A dermatoscopic image of a skin lesion.
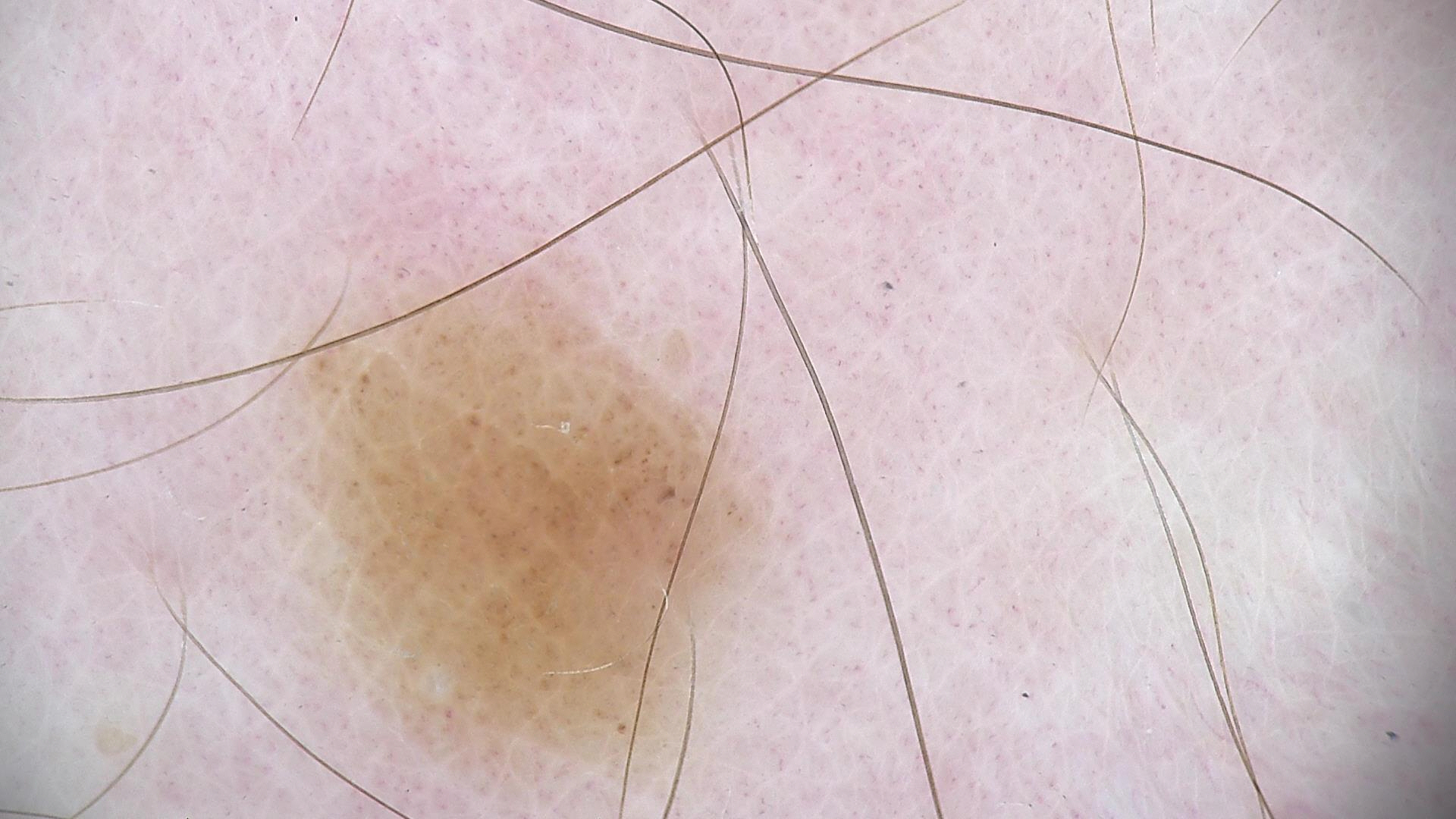  diagnosis:
    name: dysplastic junctional nevus
    code: jd
    malignancy: benign
    super_class: melanocytic
    confirmation: expert consensus